Few moles overall by the patient's own estimate · the patient reports a personal history of cancer and a personal history of skin cancer · the patient says their skin tans without first burning: 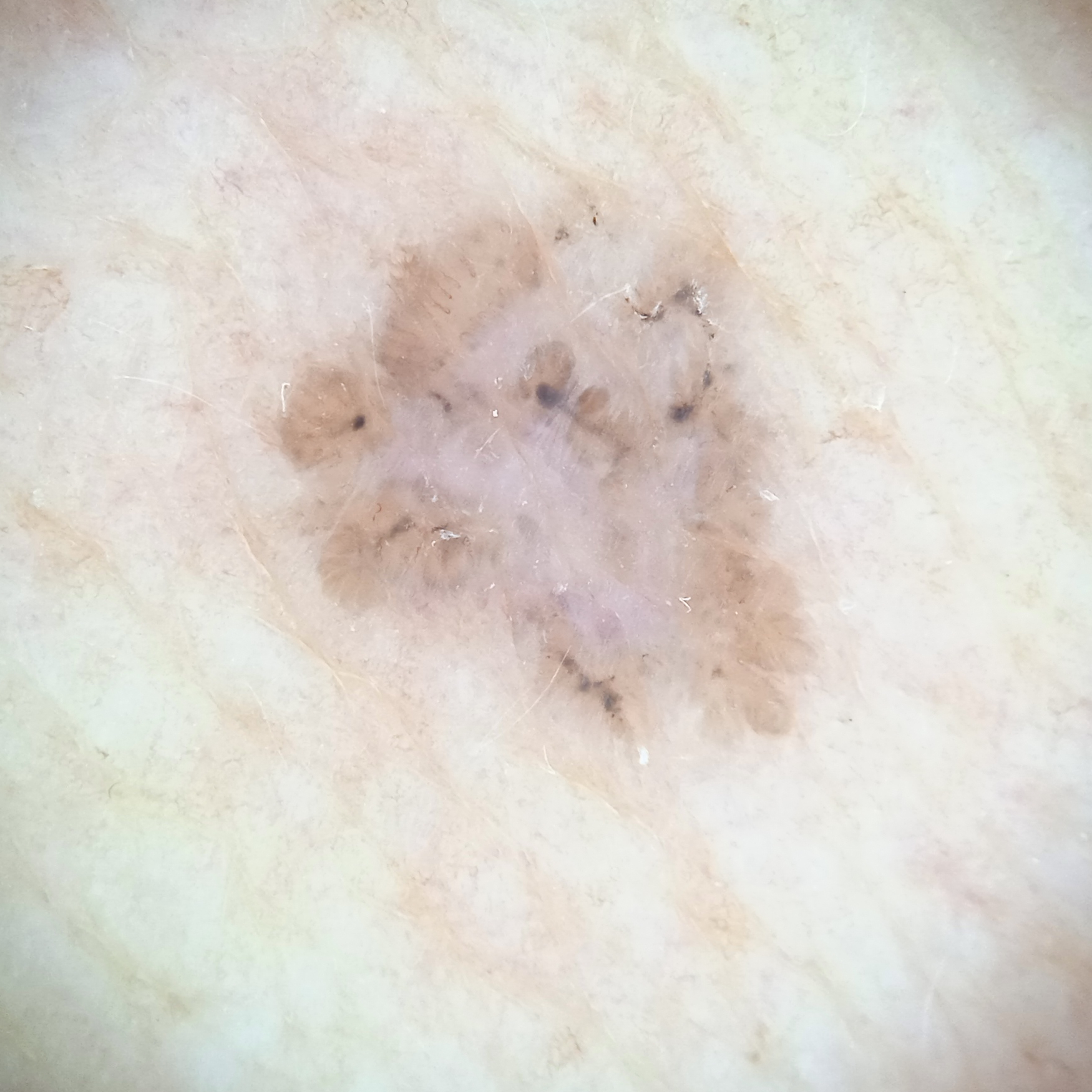Summary: The lesion is located on the torso. The lesion measures approximately 7.2 mm. Impression: The dermatologists' assessment was a basal cell carcinoma.